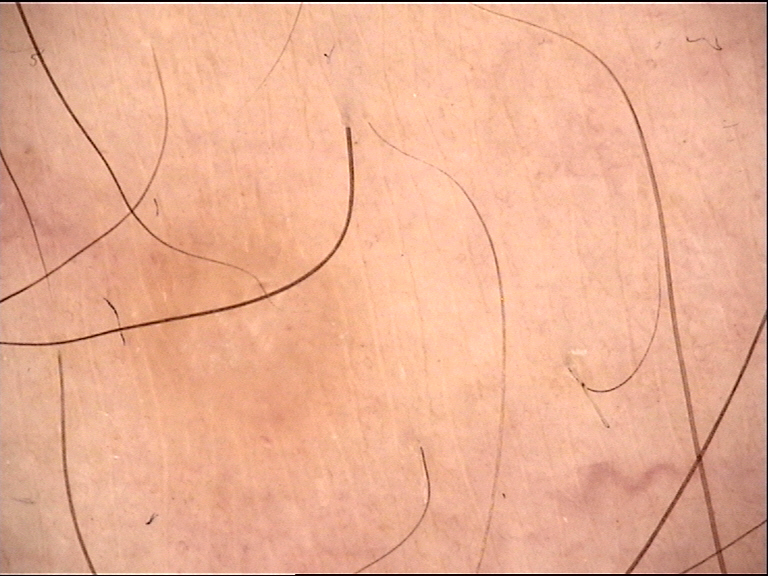{
  "image": "dermoscopy",
  "diagnosis": {
    "name": "dermatofibroma",
    "code": "df",
    "malignancy": "benign",
    "super_class": "non-melanocytic",
    "confirmation": "expert consensus"
  }
}